This image was taken at an angle · the patient is 30–39, male · located on the leg — 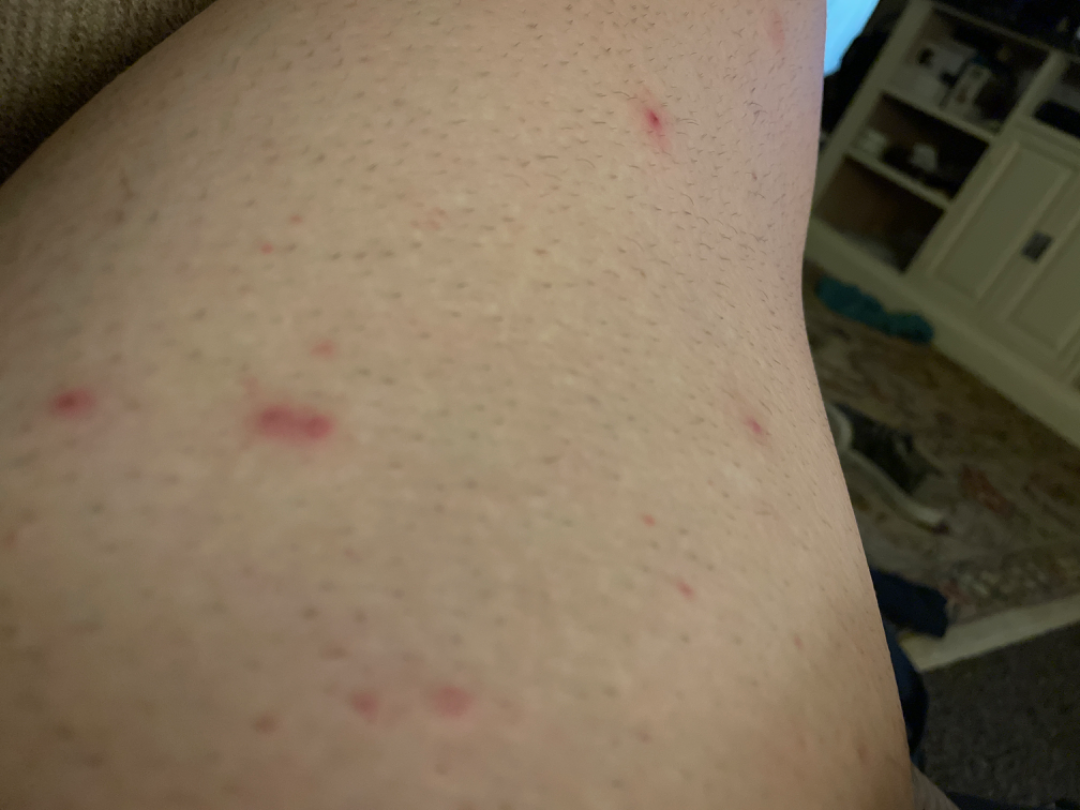Consistent with Folliculitis.